Dermoscopy of a skin lesion, a male subject aged around 70.
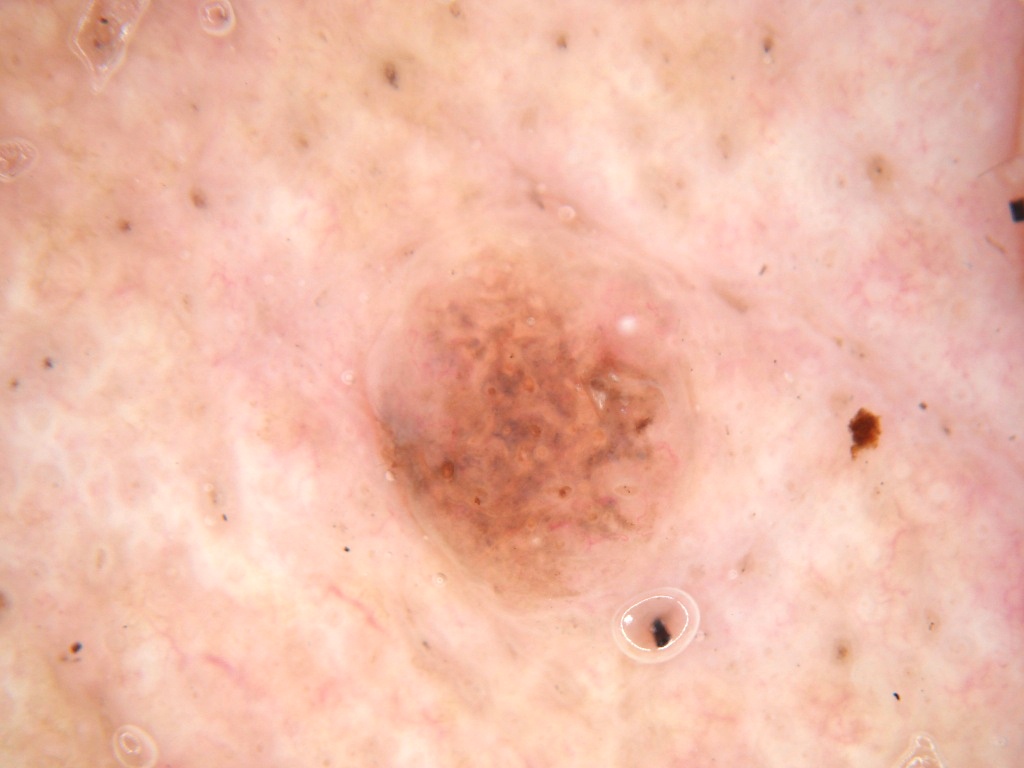lesion location = bbox=[364, 218, 698, 611] | extent = moderate | features = milia-like cysts; absent: pigment network, negative network, globules, and streaks | impression = a melanocytic nevus.